The lesion is described as flat · female subject, age 50–59 · the condition has been present for less than one week · located on the head or neck and front of the torso · this is a close-up image.
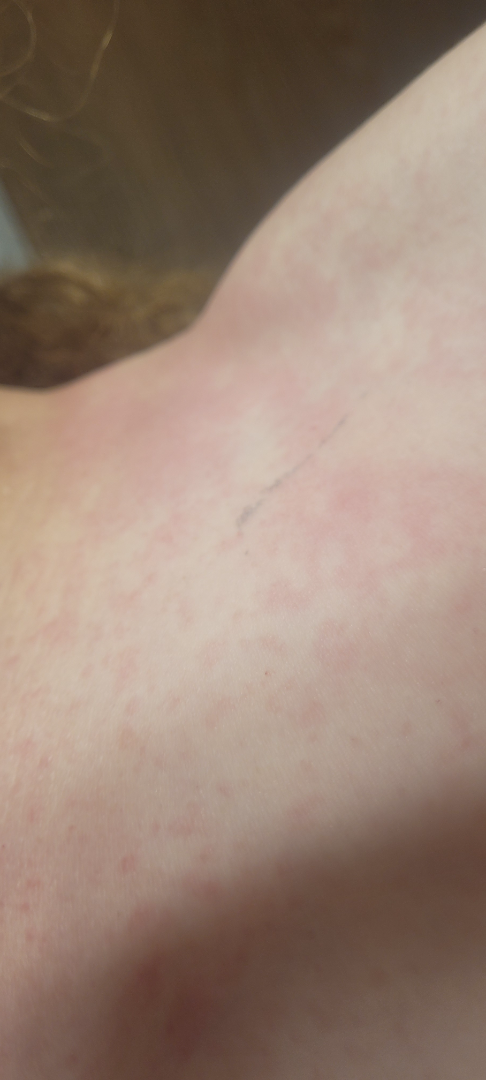{
  "assessment": "not assessable"
}